A dermoscopic close-up of a skin lesion — 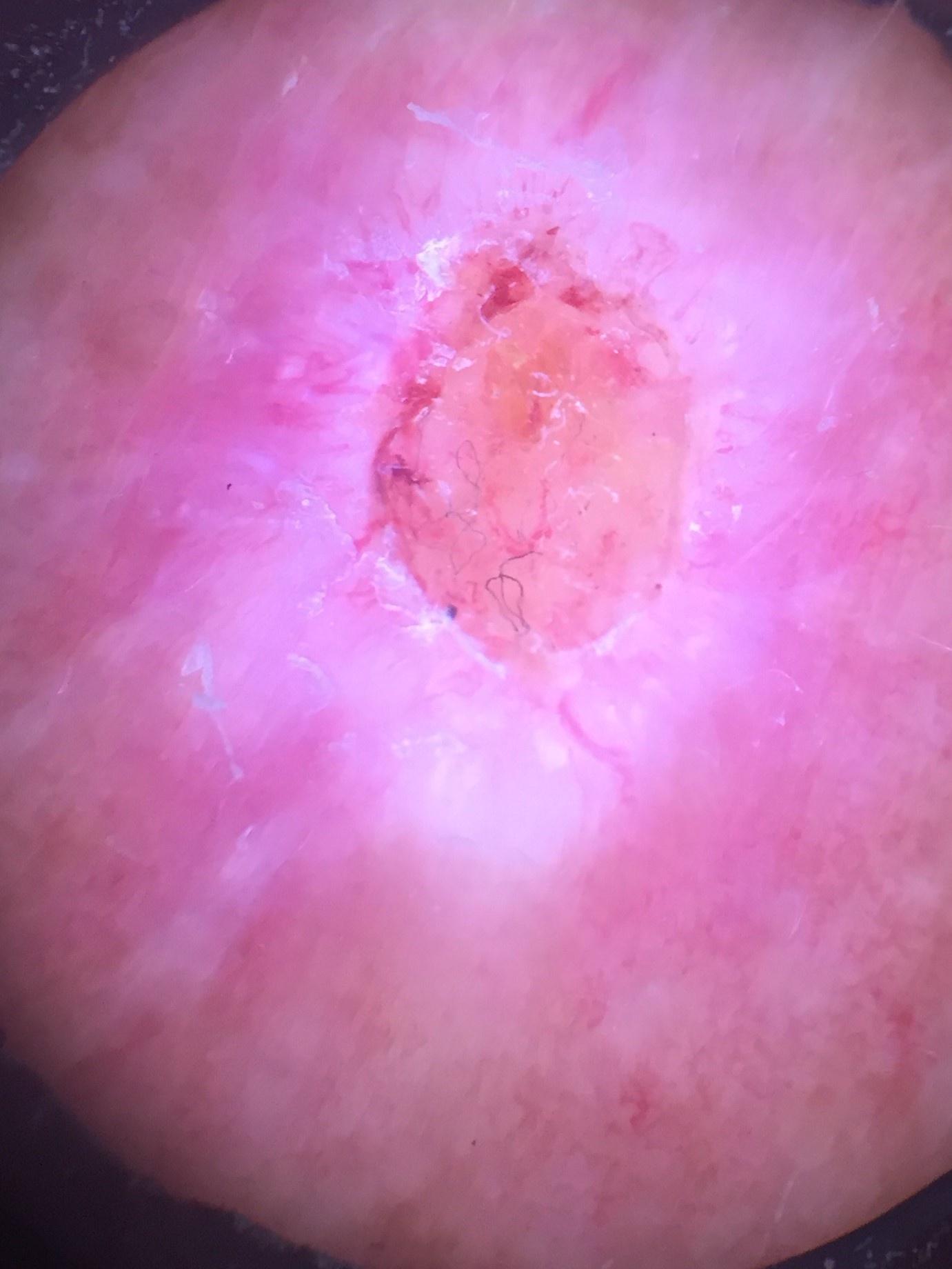<skin_lesion>
<lesion_location>
<region>the trunk</region>
<detail>the posterior trunk</detail>
</lesion_location>
<diagnosis>
<name>Basal cell carcinoma</name>
<malignancy>malignant</malignancy>
<confirmation>histopathology</confirmation>
<lineage>adnexal</lineage>
</diagnosis>
</skin_lesion>